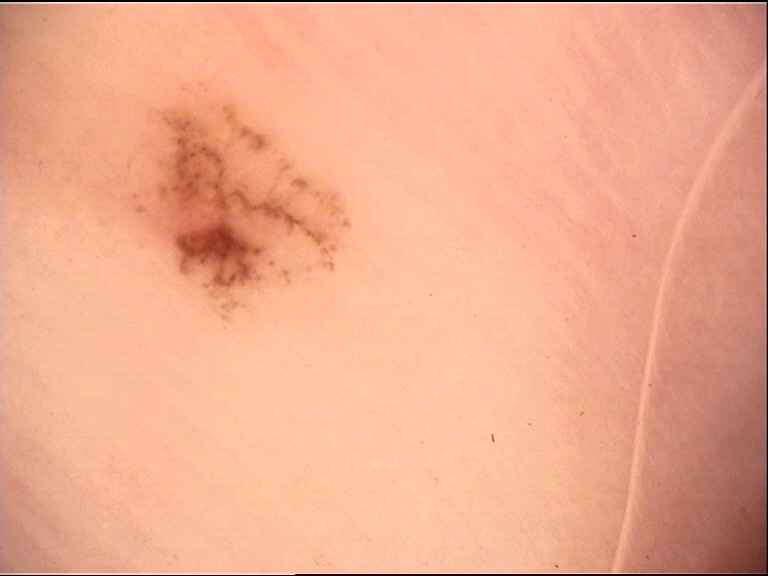Findings:
A skin lesion imaged with a dermatoscope.
Impression:
Labeled as a benign lesion — an acral dysplastic junctional nevus.